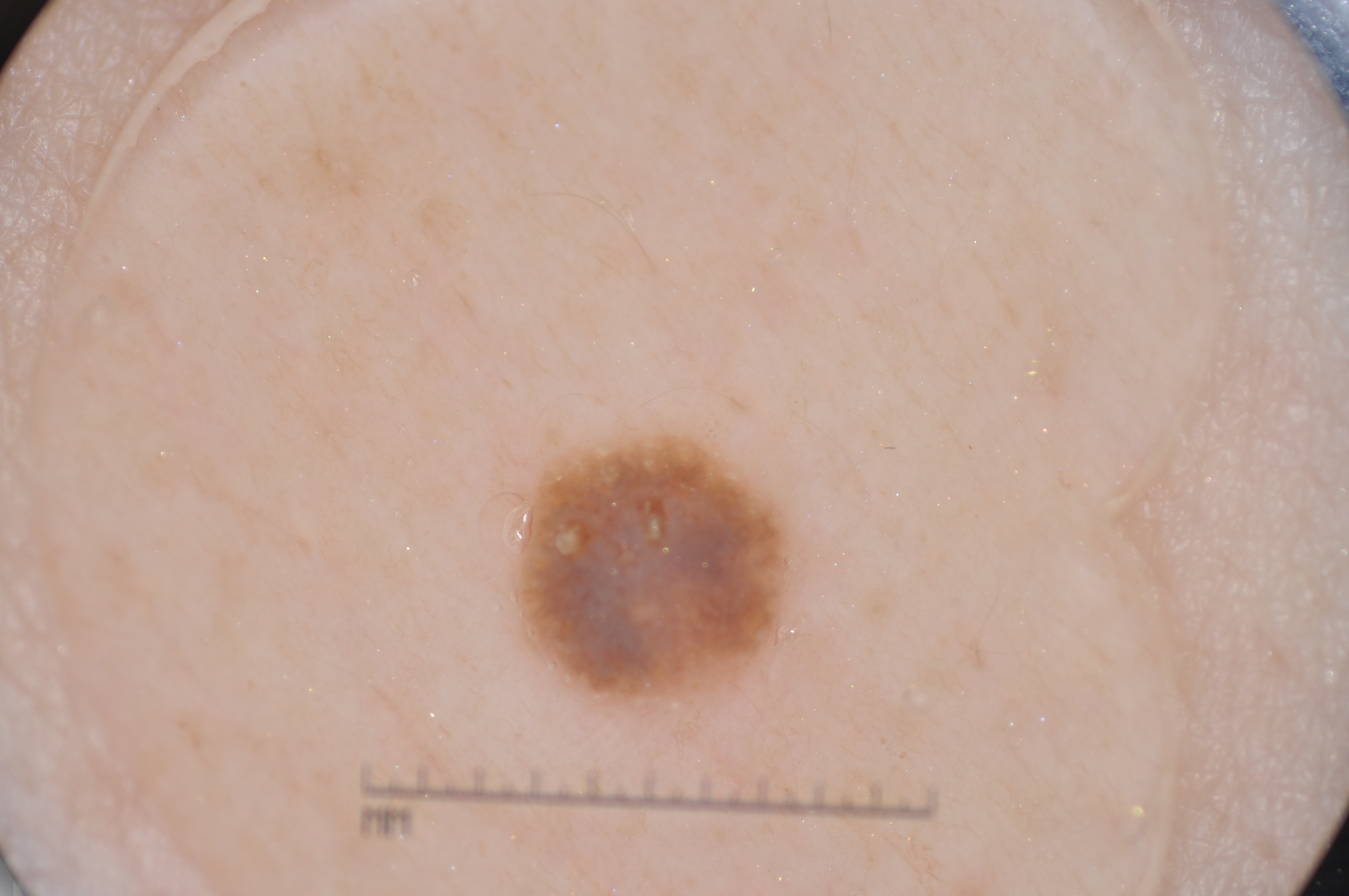A dermoscopic image of a skin lesion. A female patient approximately 50 years of age. The lesion's extent is x1=517, y1=434, x2=790, y2=707. Dermoscopically, the lesion shows milia-like cysts; no pigment network, streaks, or negative network. A small lesion within a wider field of skin. Consistent with a seborrheic keratosis, a benign skin lesion.